The photo was captured at a distance, the leg is involved — 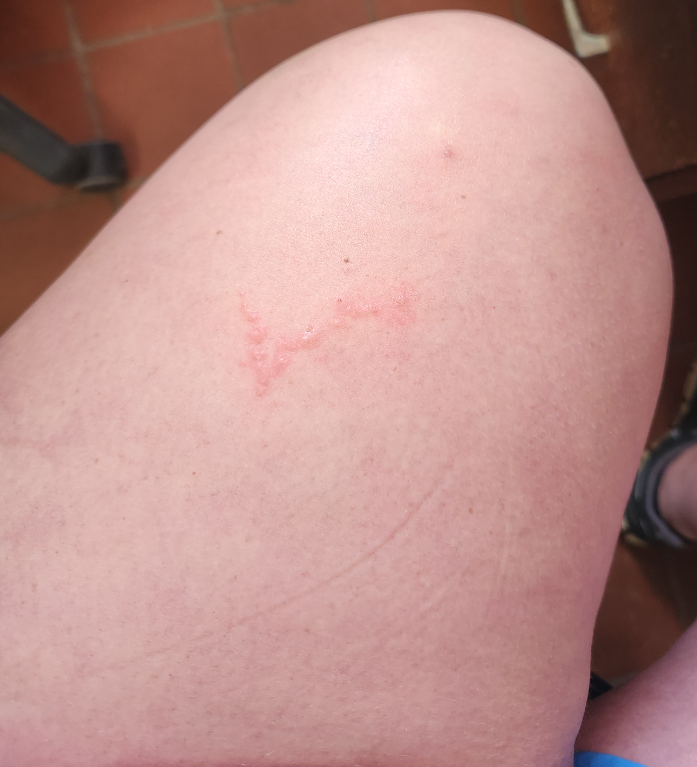The lesion is described as raised or bumpy.
No relevant systemic symptoms.
Reported lesion symptoms include itching.
Reported duration is less than one week.
Cutaneous larva migrans, Herpes Simplex and Allergic Contact Dermatitis were each considered, in no particular order.